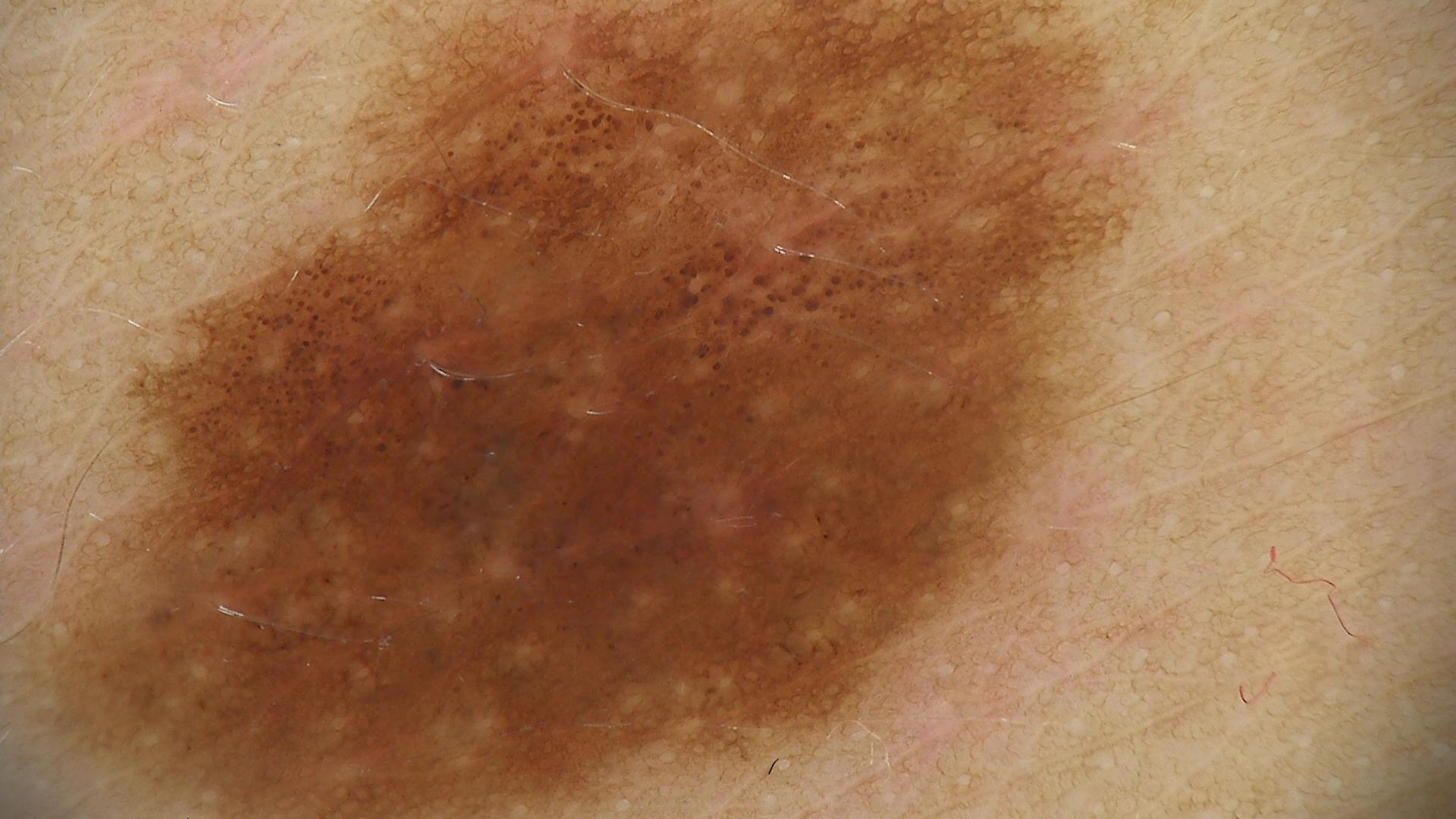The diagnostic label was a benign lesion — a dysplastic junctional nevus.